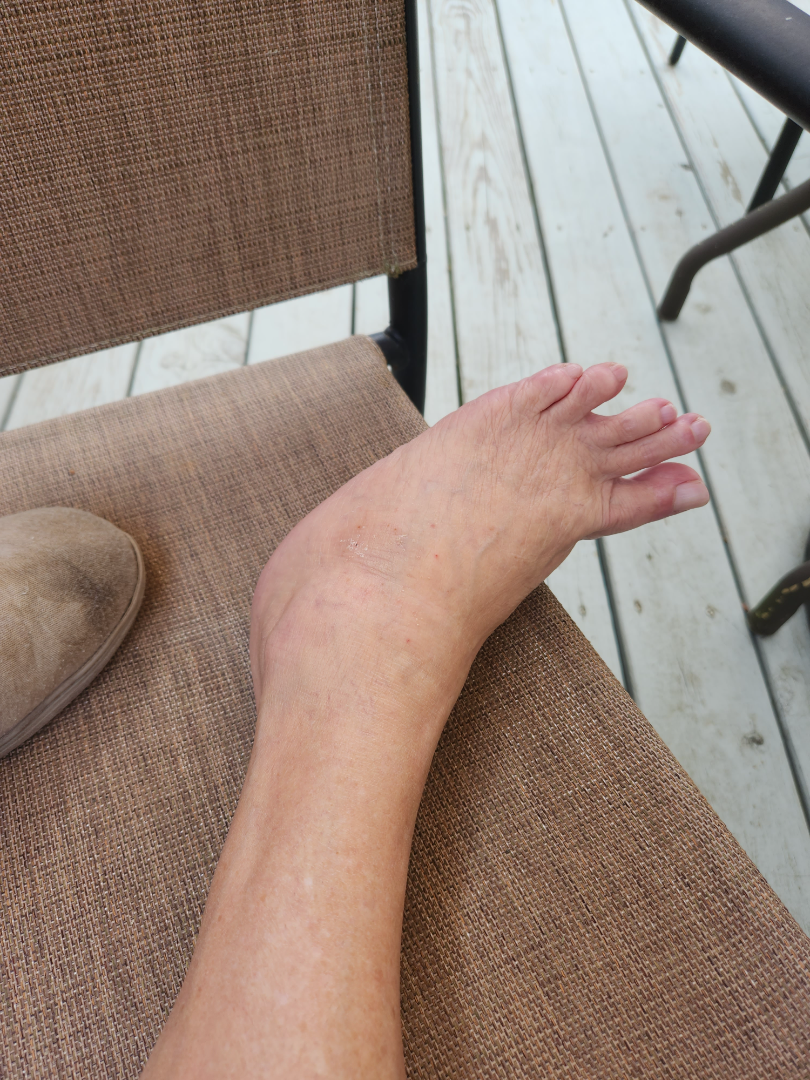Findings:
• skin tone — Fitzpatrick skin type II; non-clinician graders estimated 2 on the MST
• framing — at a distance
• assessment — Lichen Simplex Chronicus (most likely); Eczema (possible); Psoriasis (lower probability)